Present for less than one week. Reported lesion symptoms include bothersome appearance. The photograph was taken at a distance. Texture is reported as flat: 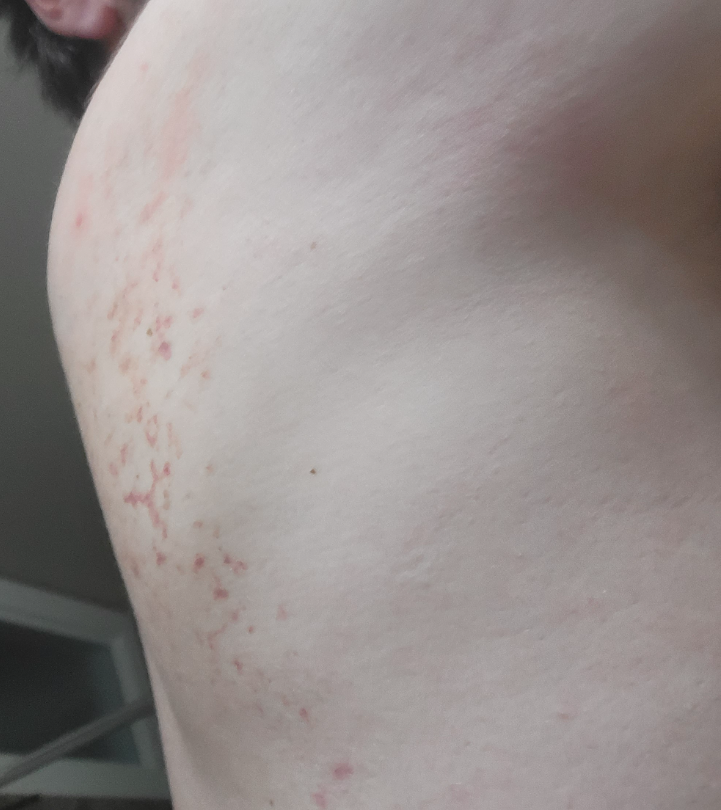No differential diagnosis could be assigned on photographic review.